The arm is involved. This image was taken at a distance. The subject is 50–59, female:
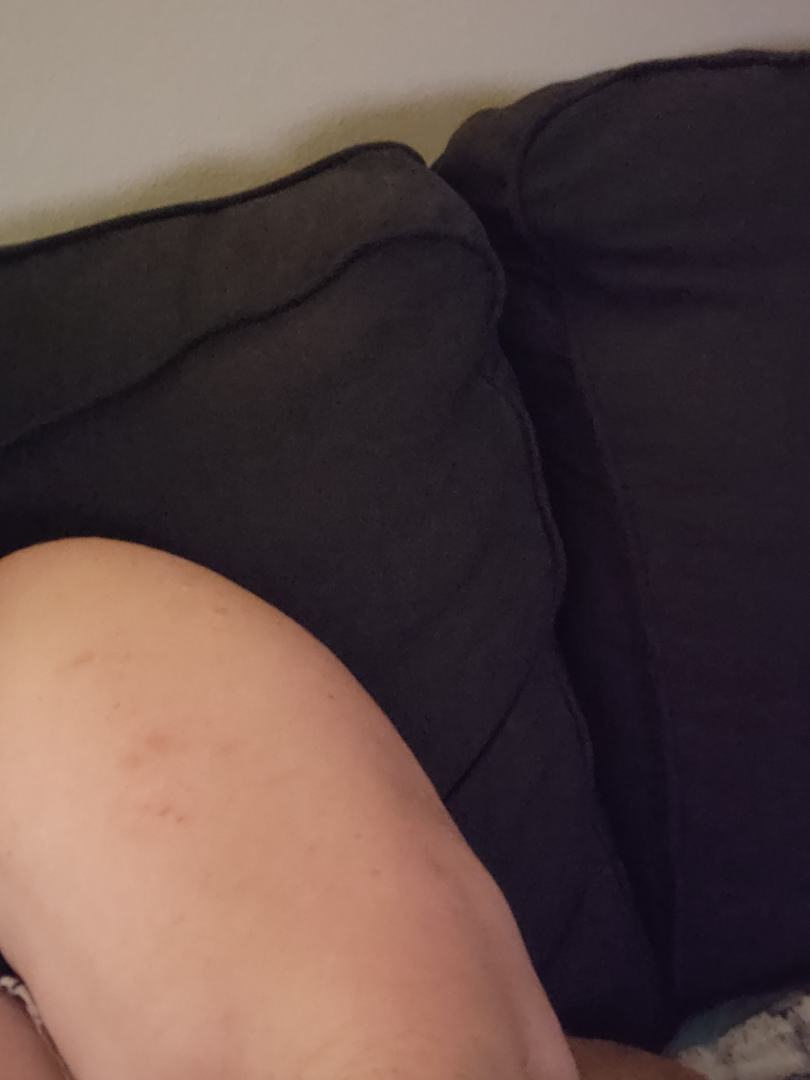  assessment: not assessable
  patient_category: a rash
  texture: raised or bumpy
  symptoms:
    - bothersome appearance
    - itching
  duration: more than one year